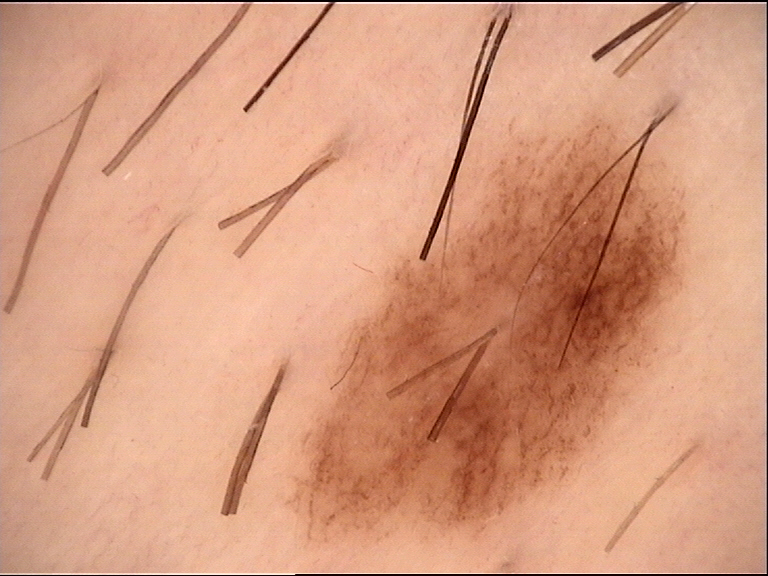The diagnosis was a dysplastic junctional nevus.